A female subject aged 58-62.
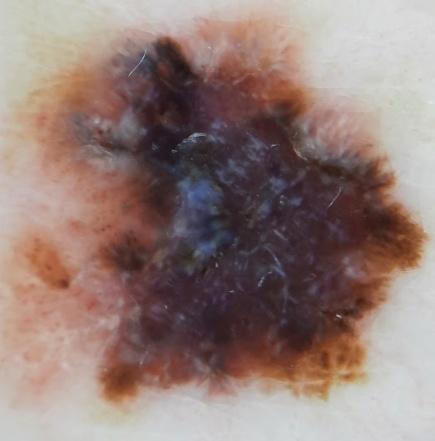{
  "diagnosis": {
    "name": "Melanoma",
    "malignancy": "malignant",
    "confirmation": "histopathology"
  }
}